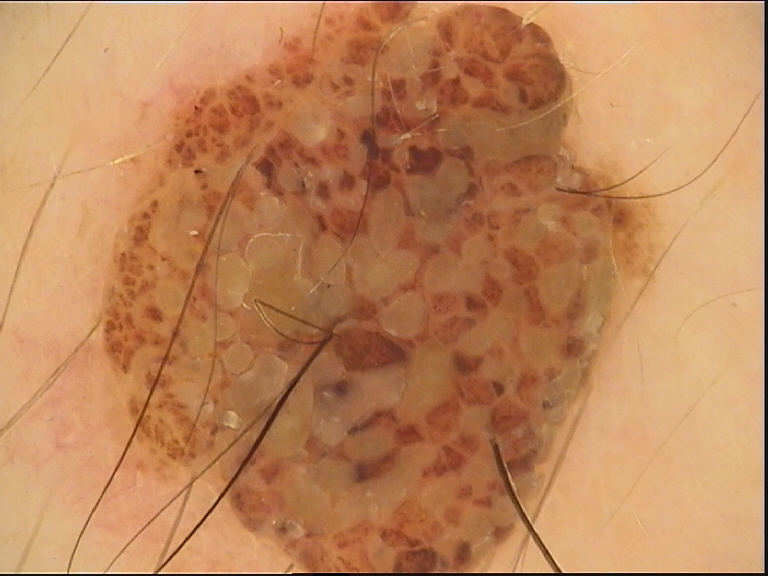Q: What is the imaging modality?
A: dermoscopy
Q: What is this lesion?
A: dermal nevus (expert consensus)